A patient 61 years old. A clinical photograph showing a skin lesion: 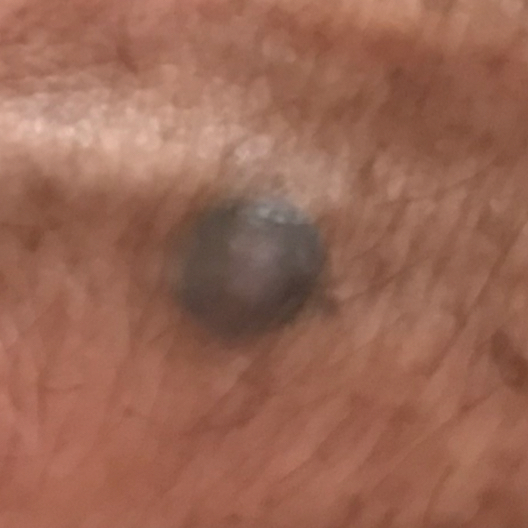lesion_location: a hand
symptoms:
  present:
    - growth
    - elevation
diagnosis:
  name: nevus
  code: NEV
  malignancy: benign
  confirmation: clinical consensus